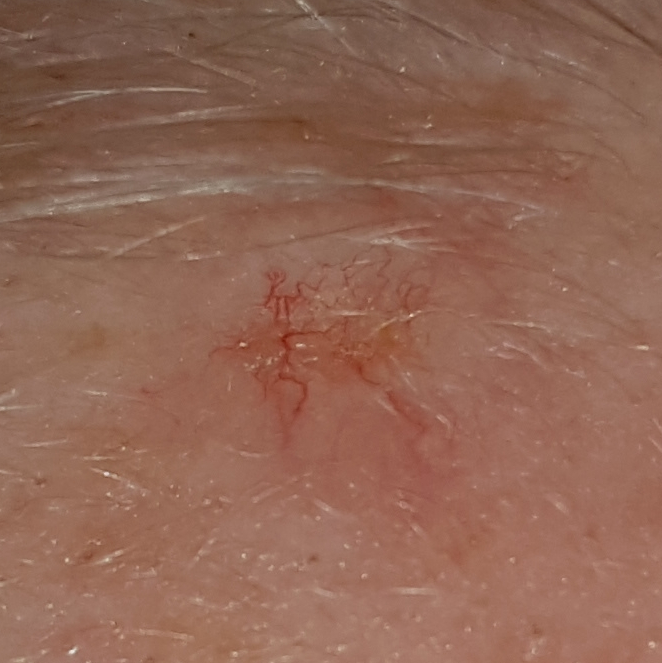{"patient": {"age": 63, "gender": "female"}, "image": "clinical photo", "skin_type": "II", "lesion_location": "the face", "lesion_size": {"diameter_1_mm": 7.0, "diameter_2_mm": 5.0}, "diagnosis": {"name": "basal cell carcinoma", "code": "BCC", "malignancy": "malignant", "confirmation": "histopathology"}}